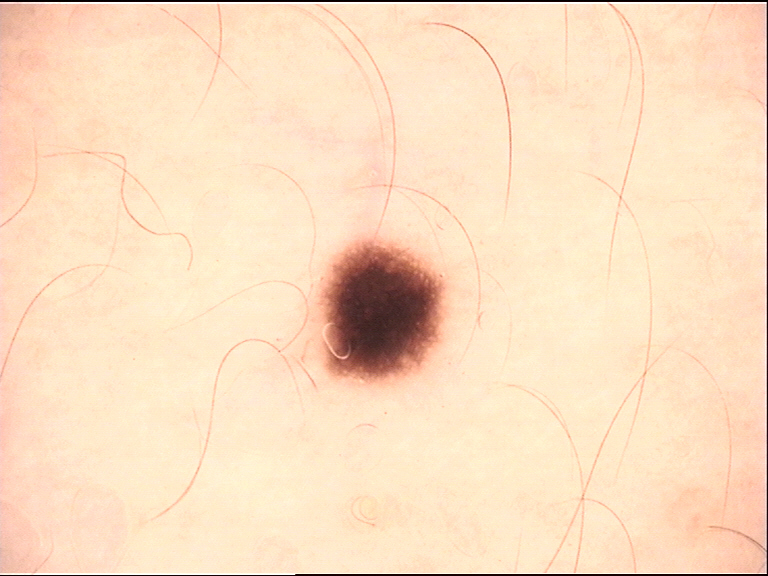Findings: A dermoscopy image of a single skin lesion. Impression: Labeled as a dysplastic junctional nevus.